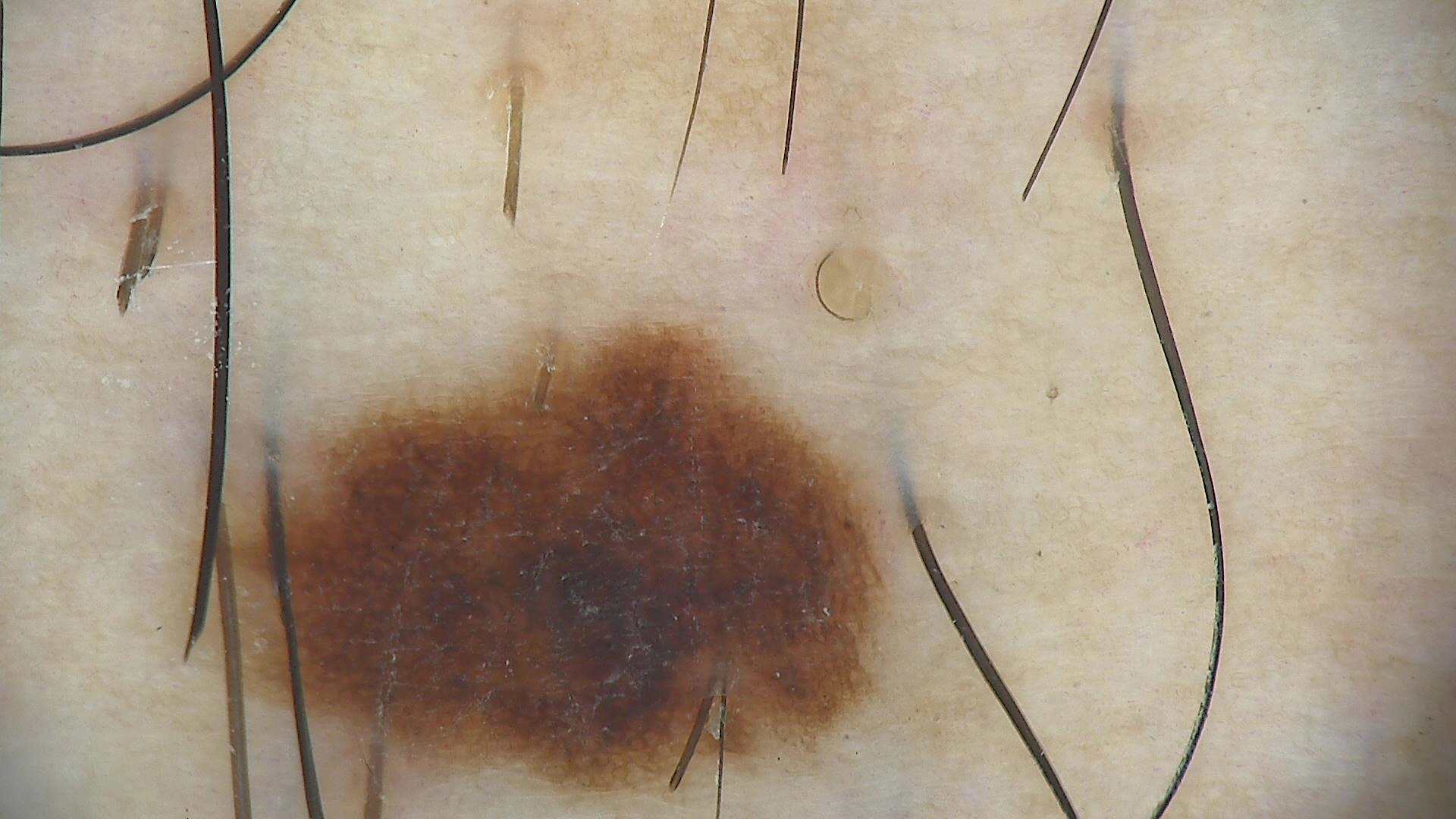Labeled as a dysplastic junctional nevus.